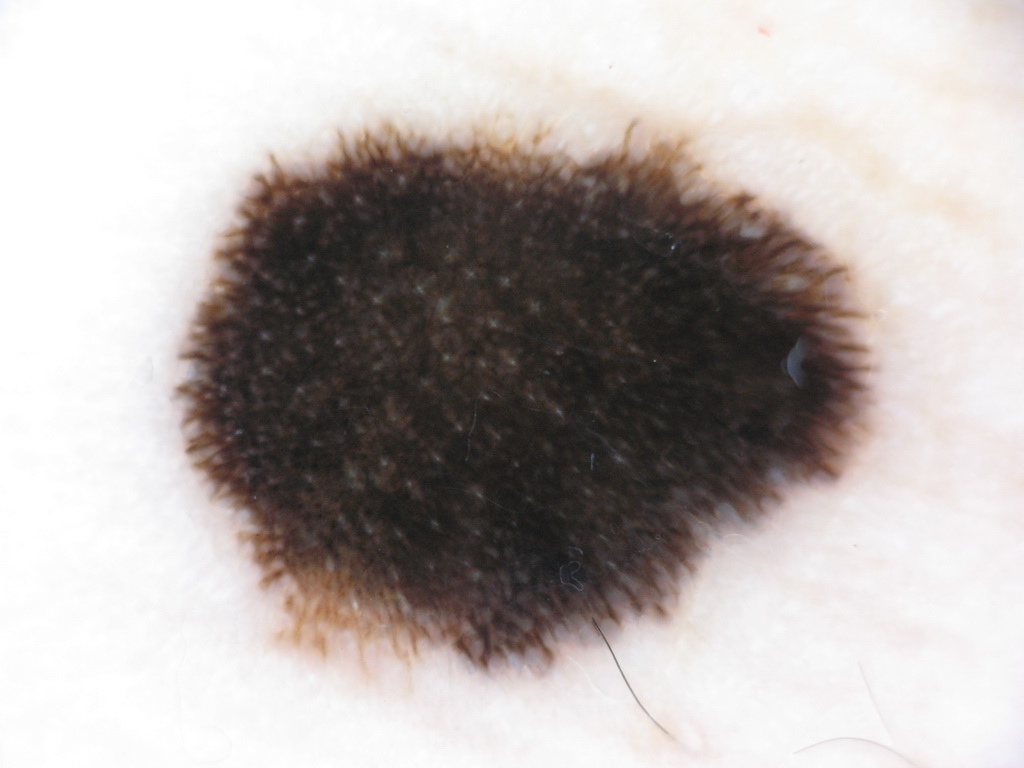Image and clinical context:
A dermoscopic view of a skin lesion. A female subject, roughly 5 years of age. The lesion takes up about 41% of the image. Dermoscopy demonstrates pigment network, milia-like cysts, and streaks; no negative network. With coordinates (x1, y1, x2, y2), lesion location: <bbox>169, 109, 891, 687</bbox>.
Impression:
The diagnostic assessment was a melanocytic nevus, a benign lesion.